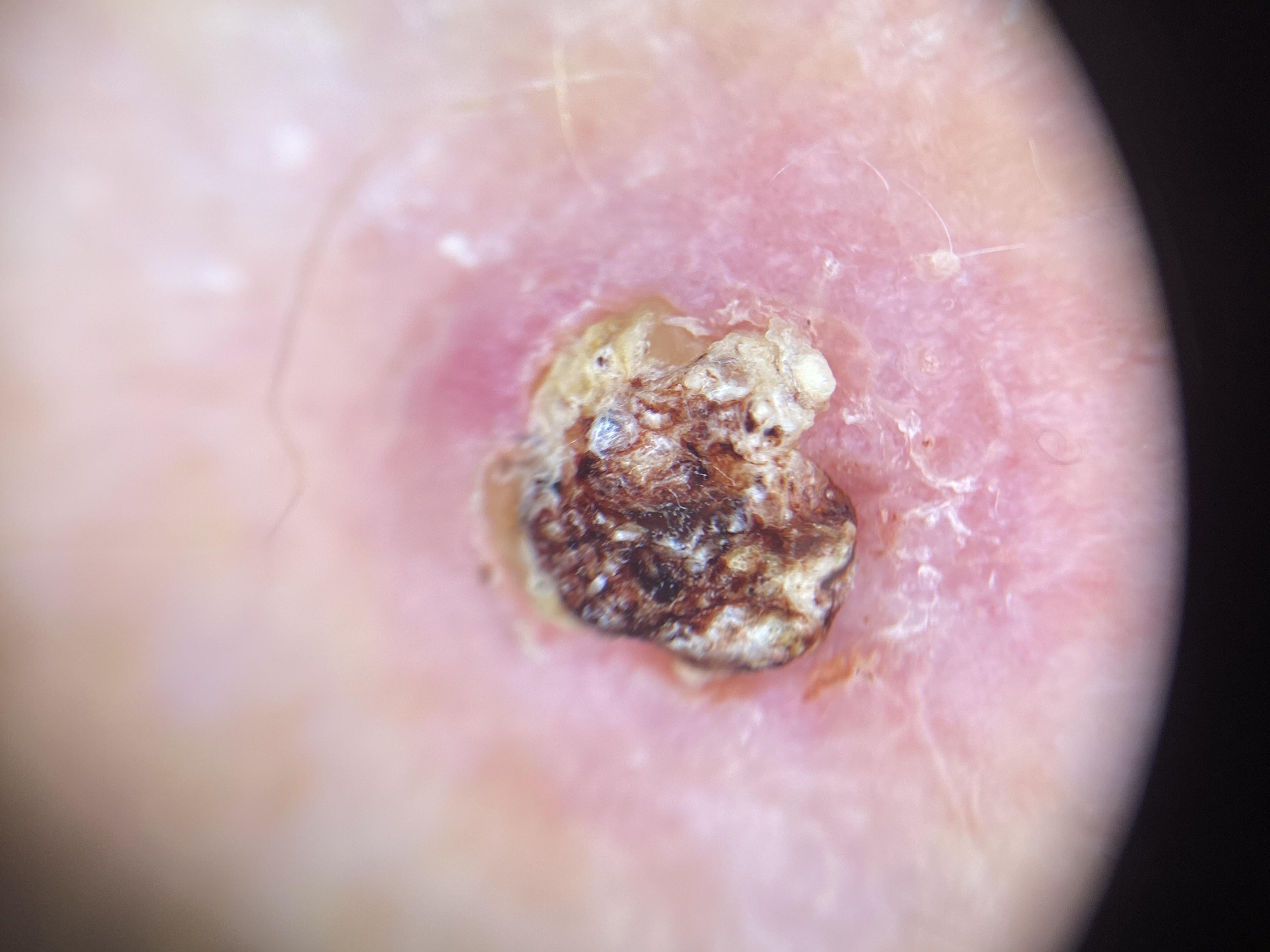A male patient aged around 75. Histopathological examination showed a malignancy — a squamous cell carcinoma.